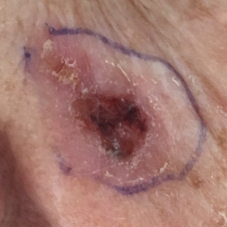<case>
  <patient>
    <age>66</age>
    <gender>female</gender>
  </patient>
  <image>clinical photograph</image>
  <diagnosis>
    <name>basal cell carcinoma</name>
    <code>BCC</code>
    <malignancy>malignant</malignancy>
    <confirmation>histopathology</confirmation>
  </diagnosis>
</case>